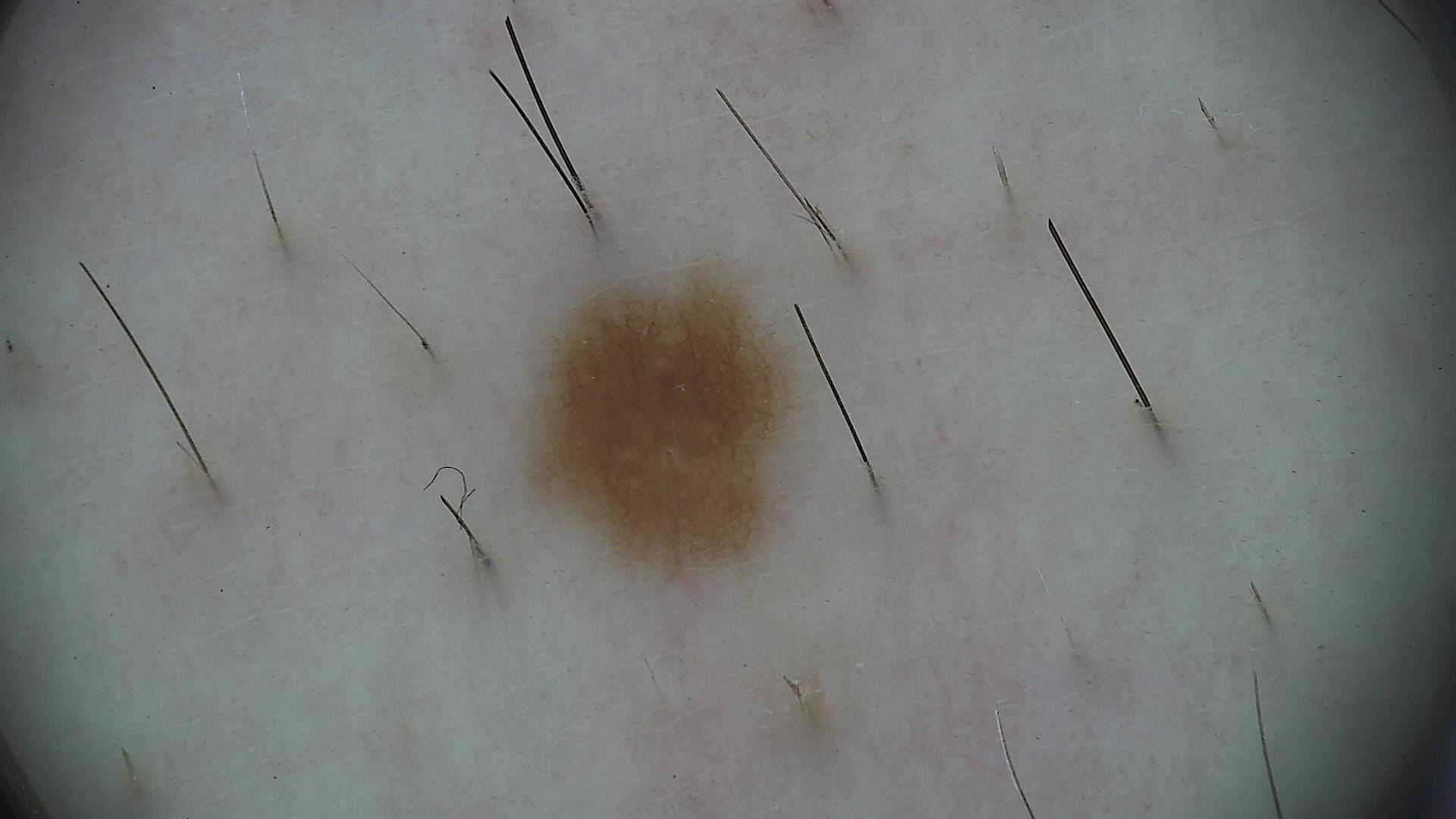Diagnosed as a banal lesion — a junctional nevus.